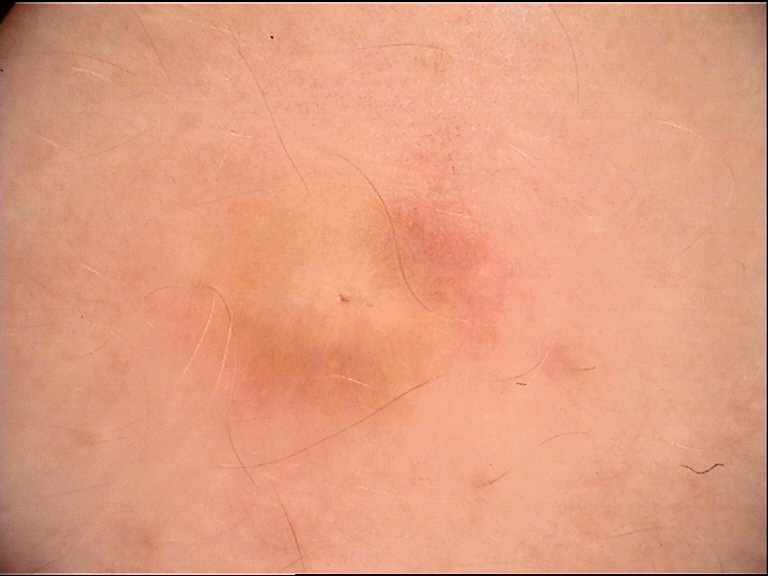imaging — dermoscopy
category — fibro-histiocytic
assessment — dermatofibroma (expert consensus)